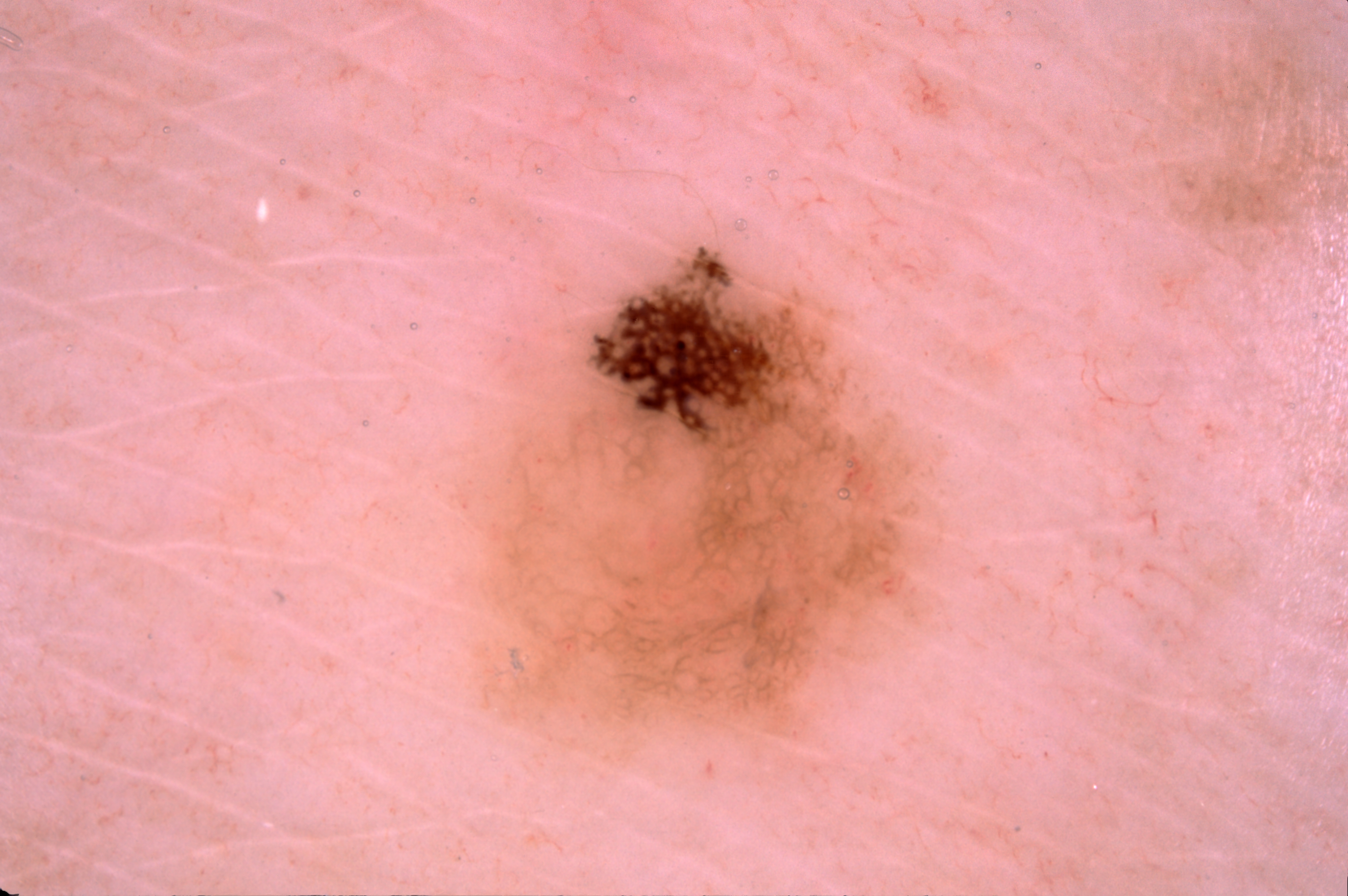Image and clinical context: The subject is a male approximately 60 years of age. A dermoscopic view of a skin lesion. The lesion takes up about 16% of the image. Dermoscopically, the lesion shows pigment network. In (x1, y1, x2, y2) order, the lesion is bounded by box(447, 209, 949, 767). Conclusion: Expert review diagnosed this as a melanocytic nevus.